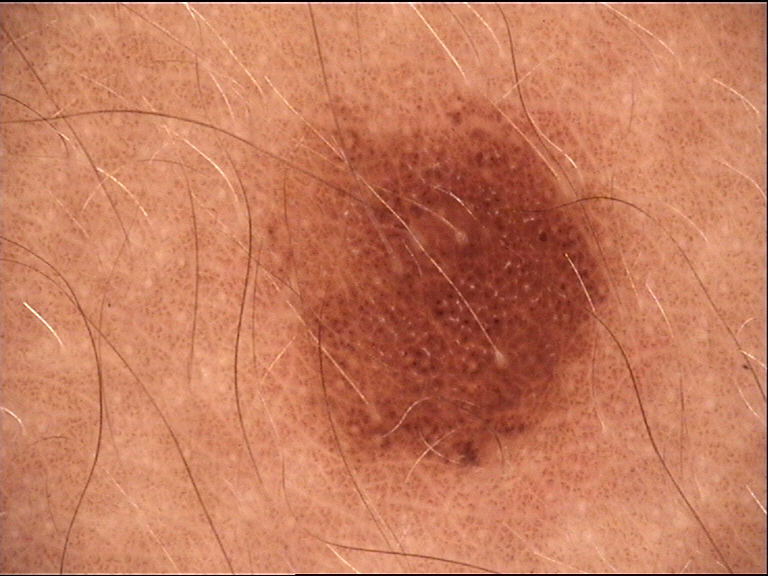Dermoscopy of a skin lesion.
The diagnosis was a dysplastic junctional nevus.